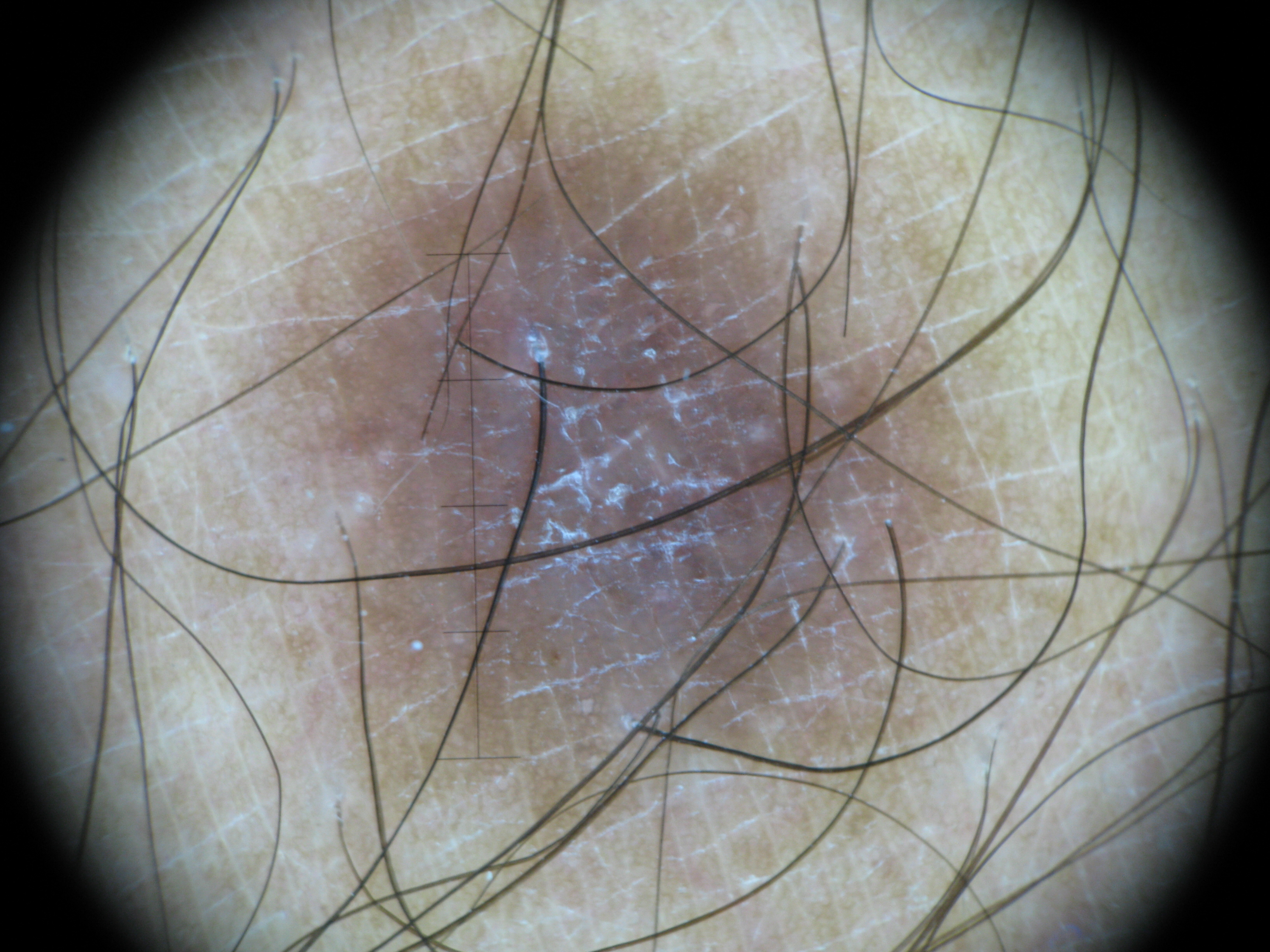Summary: A dermoscopic image of a skin lesion. This is a fibro-histiocytic lesion. Impression: Classified as a dermatofibroma.